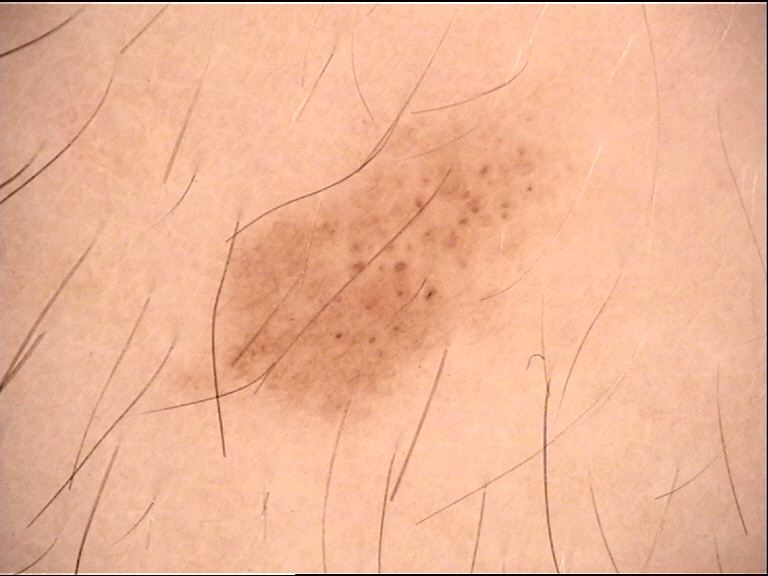A dermoscopic close-up of a skin lesion.
The morphology is that of a banal lesion.
Labeled as a congenital compound nevus.